A dermatoscopic image of a skin lesion.
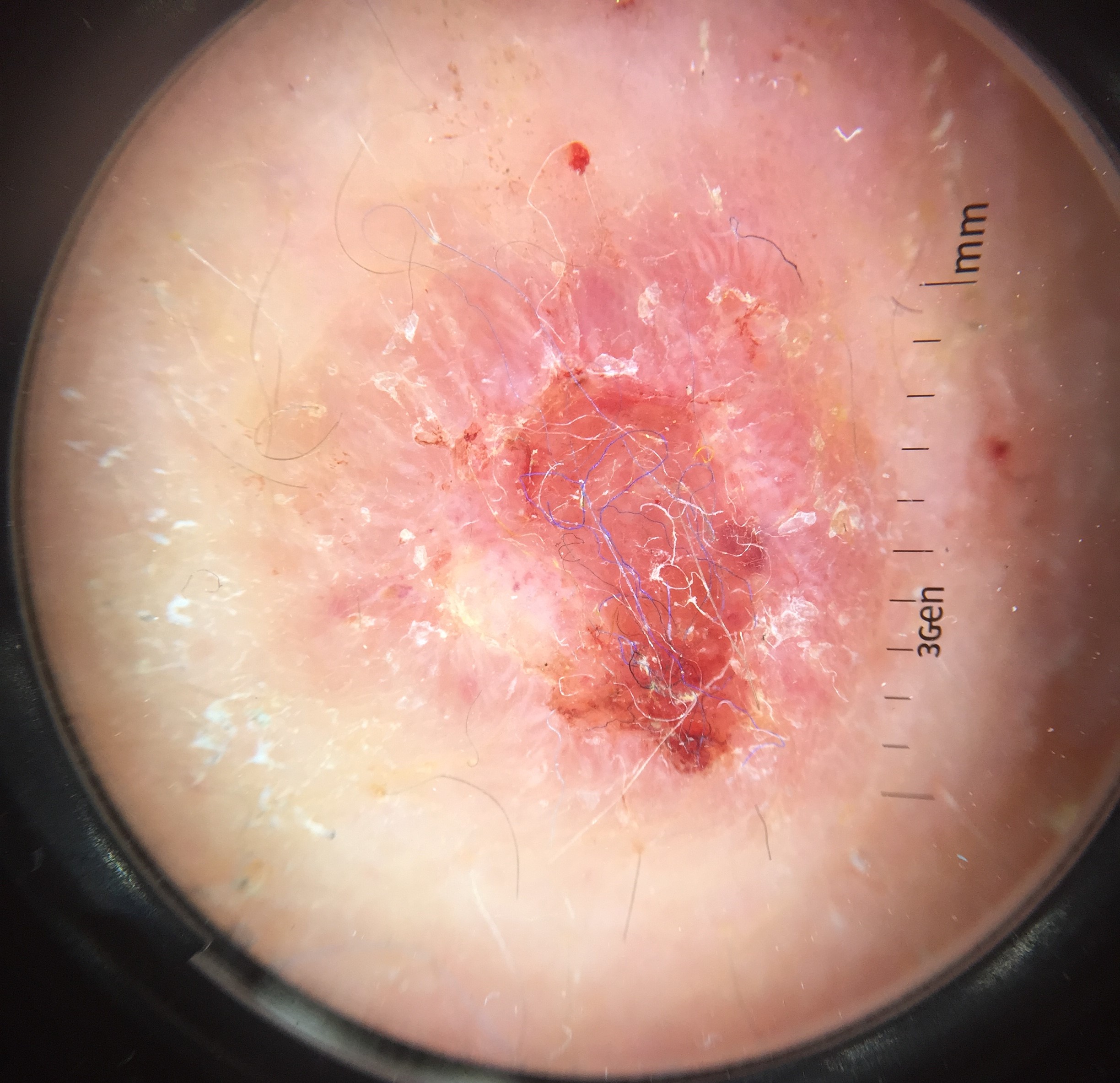Conclusion:
Histopathologically confirmed as a keratinocytic, malignant lesion — a squamous cell carcinoma.